A dermoscopy image of a single skin lesion.
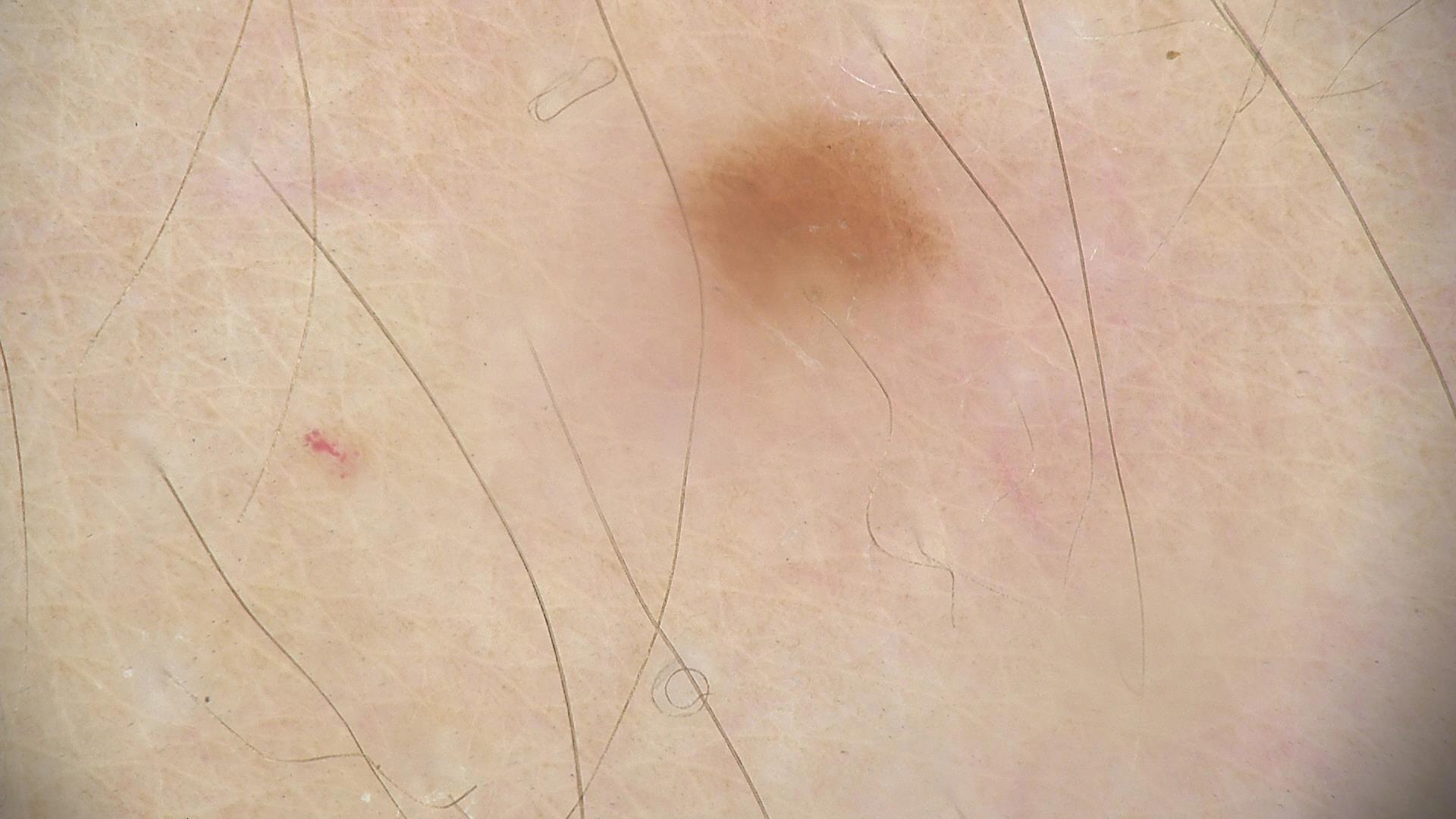Consistent with a dysplastic junctional nevus.